The subject is male. The front of the torso is involved. An image taken at a distance — 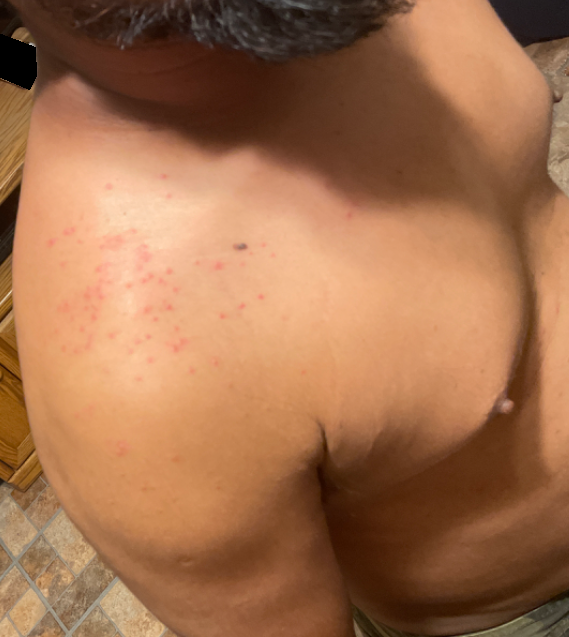Q: What was the assessment?
A: ungradable on photographic review